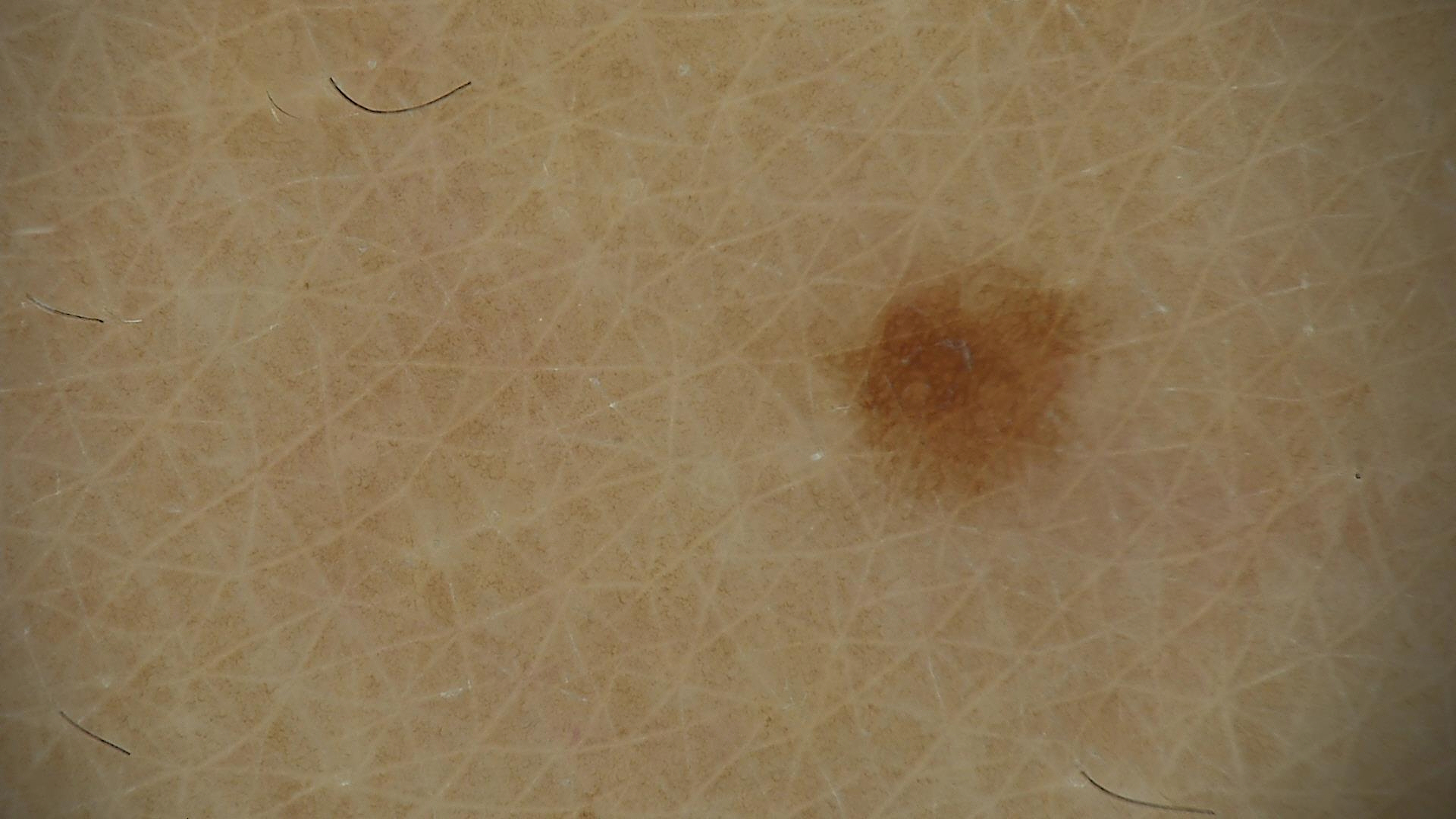A dermoscopic close-up of a skin lesion. Labeled as a dysplastic junctional nevus.